Dermoscopy of a skin lesion.
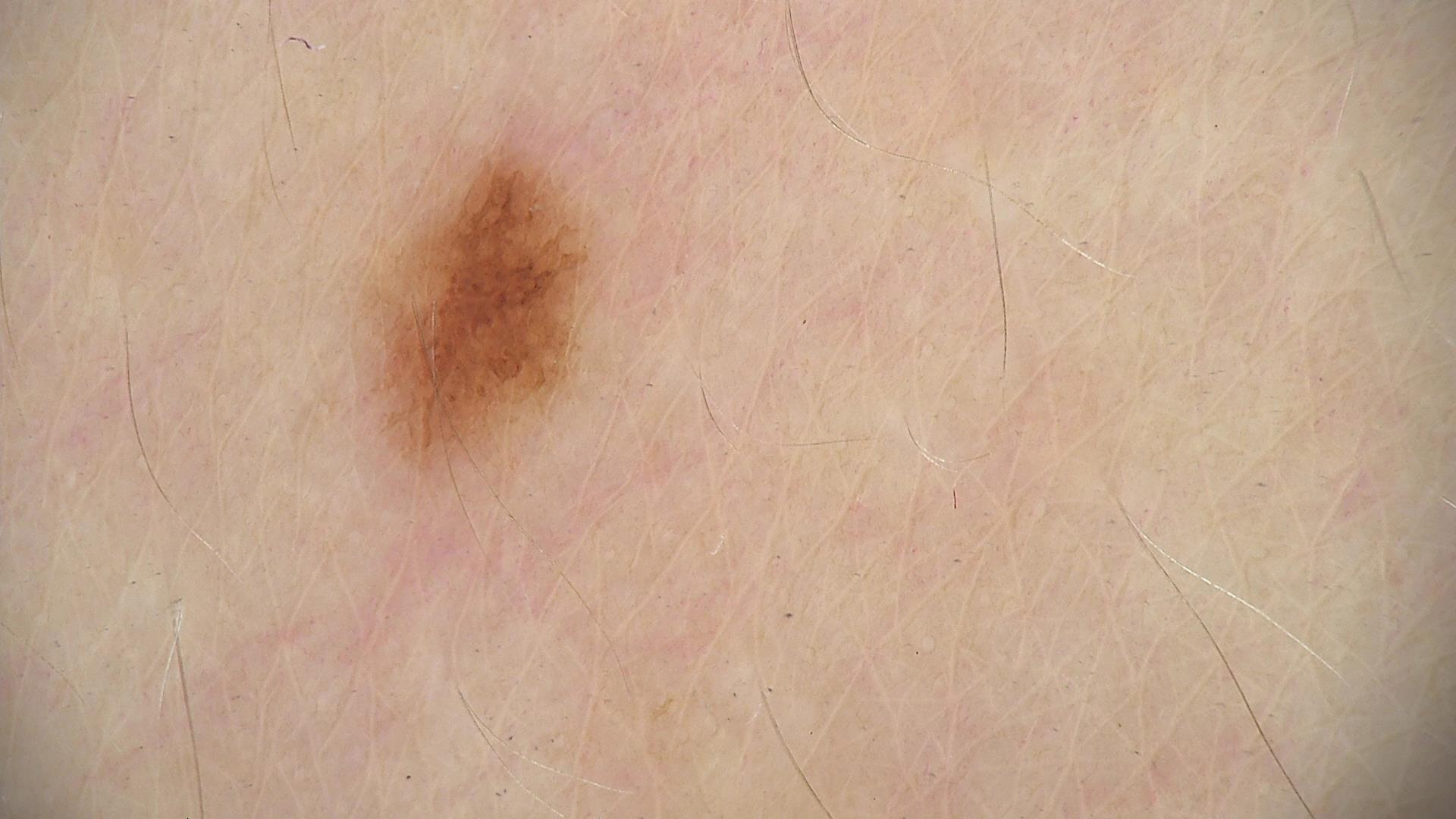The diagnosis was a benign lesion — a dysplastic junctional nevus.